The patient is 18–29, male · the affected area is the leg · the photograph is a close-up of the affected area: 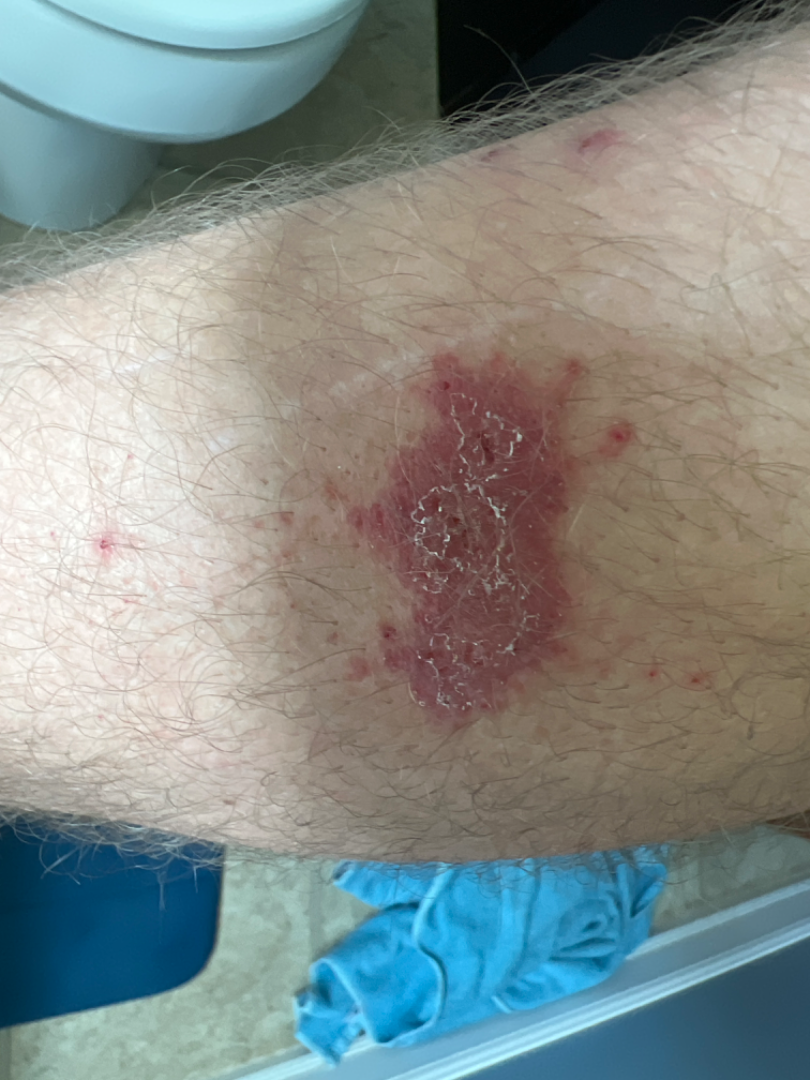<summary>
  <assessment>ungradable on photographic review</assessment>
  <symptoms>itching</symptoms>
  <duration>less than one week</duration>
  <texture>raised or bumpy</texture>
  <patient_category>a rash</patient_category>
</summary>